This image was taken at a distance:
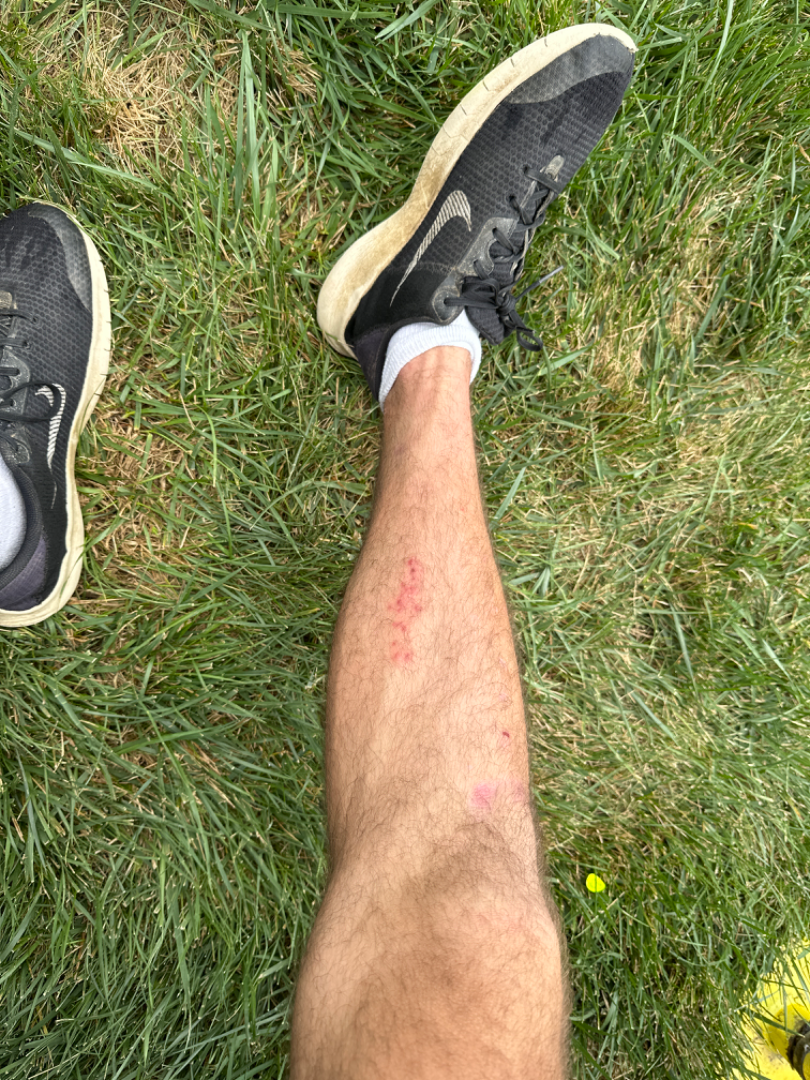Case summary:
- differential: Folliculitis, Eczema and Allergic Contact Dermatitis were considered with similar weight